Reported lesion symptoms include itching; the contributor notes the lesion is raised or bumpy; no associated systemic symptoms reported; an image taken at an angle: 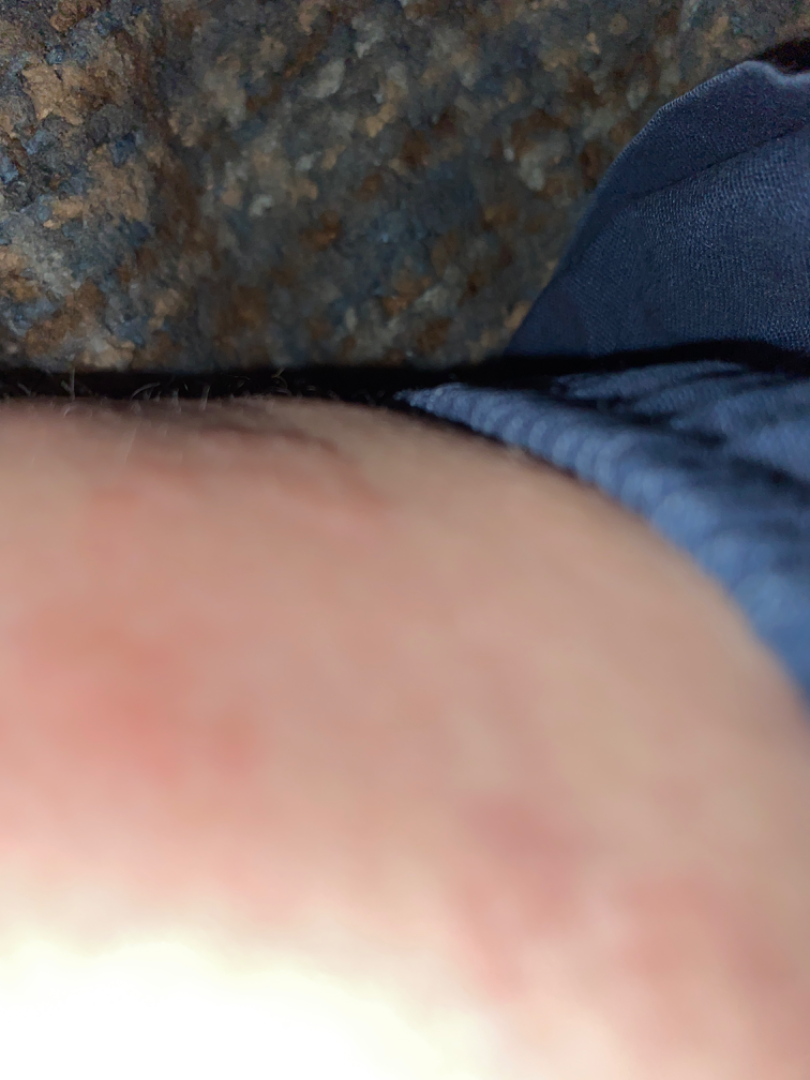On remote dermatologist review: in keeping with Urticaria.